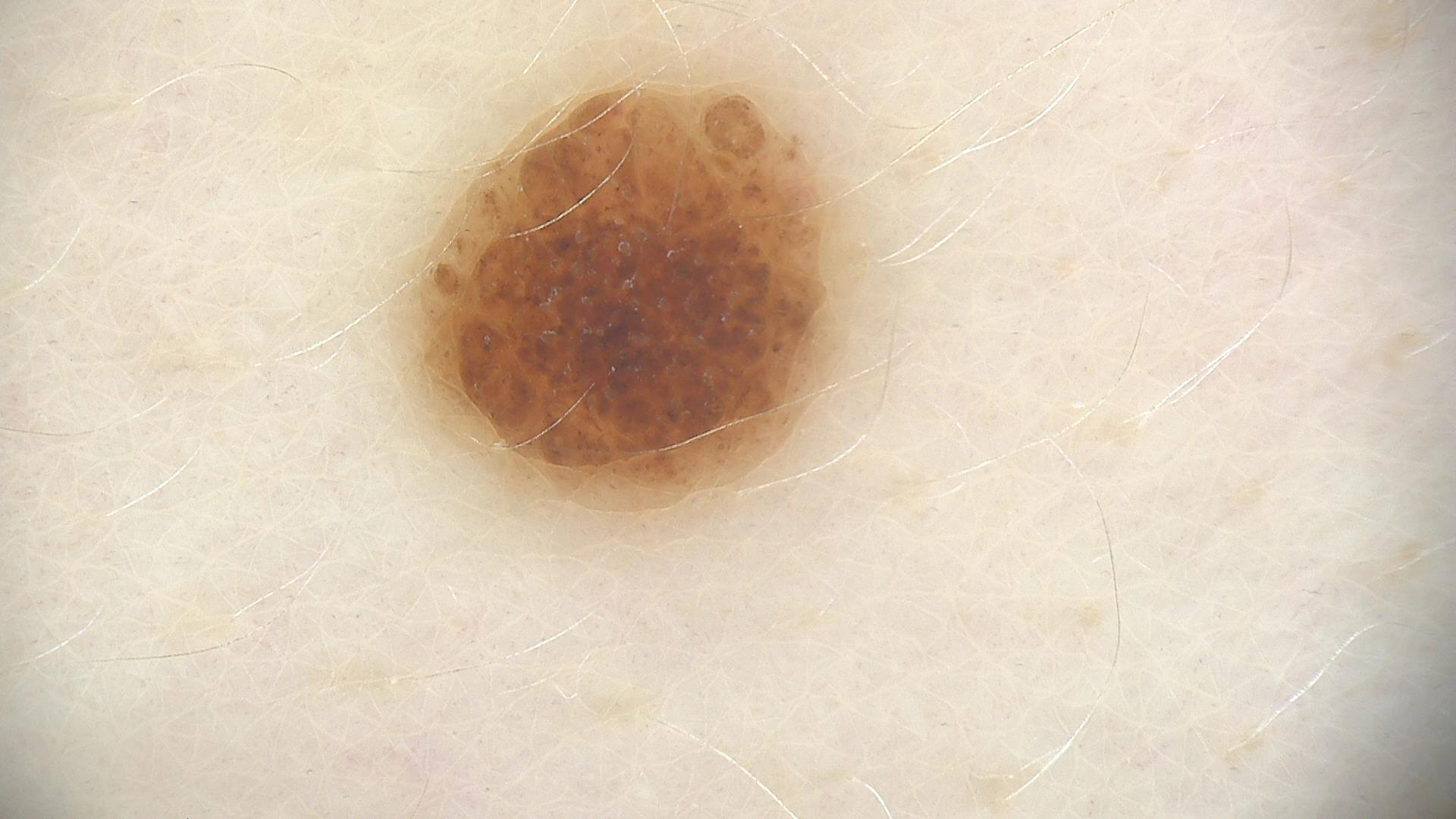A dermoscopy image of a single skin lesion. Diagnosed as a banal lesion — a compound nevus.